A dermatoscopic image of a skin lesion.
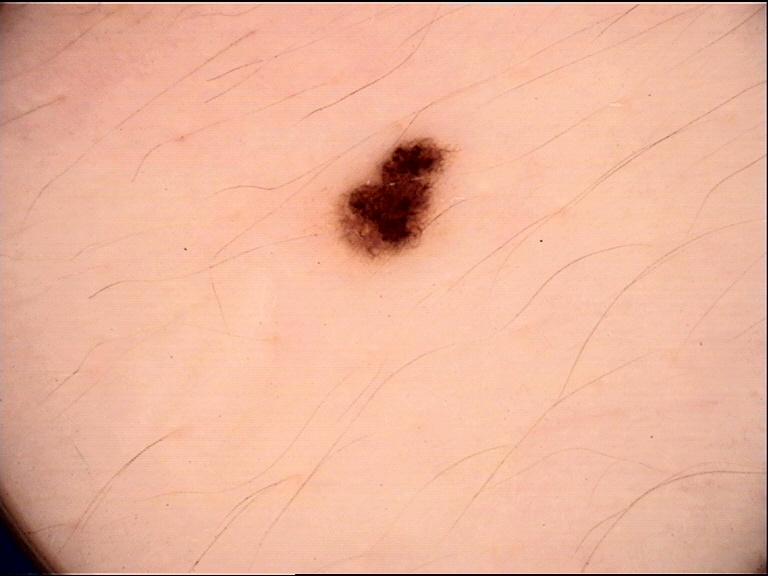| feature | finding |
|---|---|
| diagnostic label | dysplastic junctional nevus (expert consensus) |